The leg, back of the hand, top or side of the foot and arm are involved. An image taken at a distance.
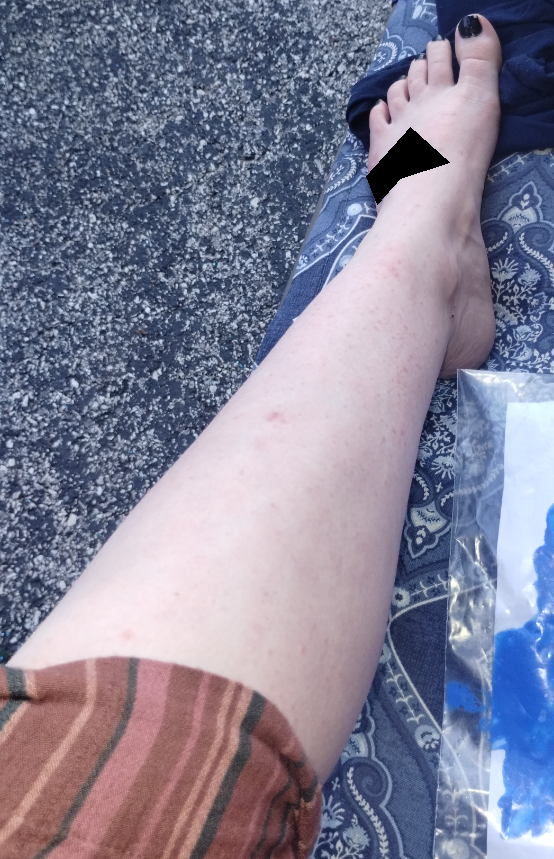| field | value |
|---|---|
| surface texture | rough or flaky and raised or bumpy |
| symptoms | itching |
| patient's own categorization | a rash |
| assessment | Folliculitis and Vasculitis of the skin were each considered, in no particular order |